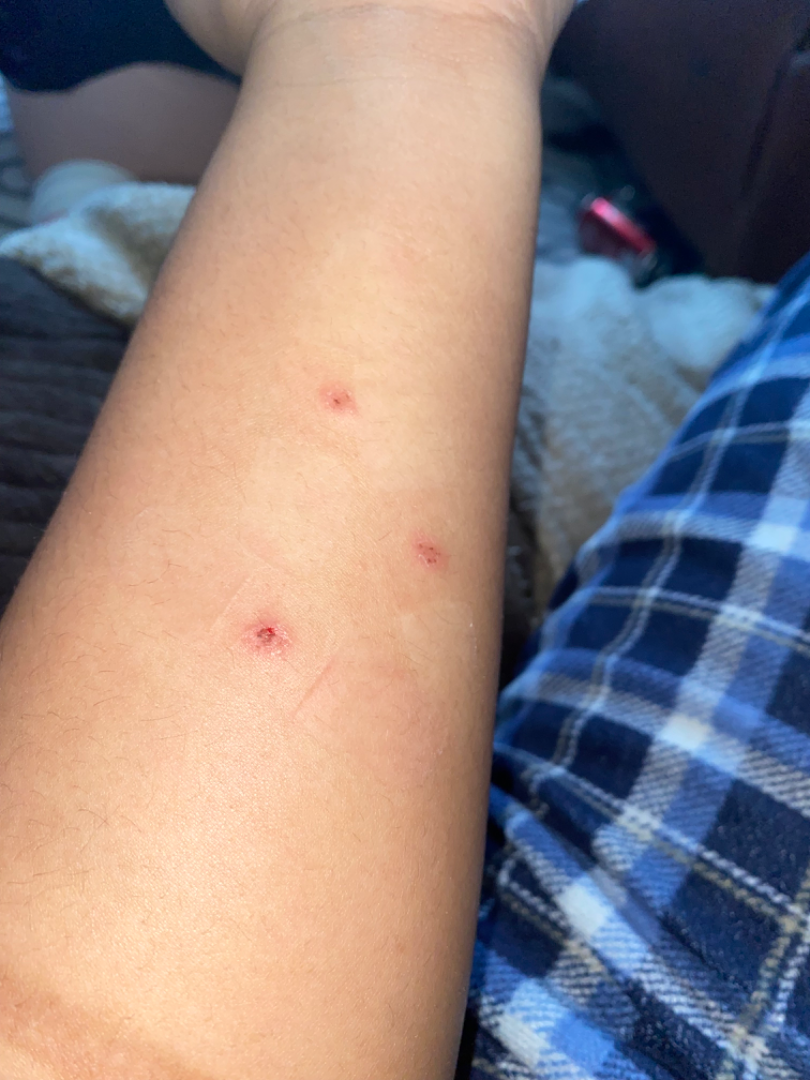photo taken: at a distance
lesion symptoms: burning, itching, pain and bothersome appearance
self-categorized as: a rash
duration: less than one week
surface texture: rough or flaky
skin tone: Fitzpatrick phototype V; non-clinician graders estimated Monk skin tone scale 4 or 5 (two reviewer pools)
affected area: head or neck and arm
diagnostic considerations: Acne (favored); Impetigo (considered)